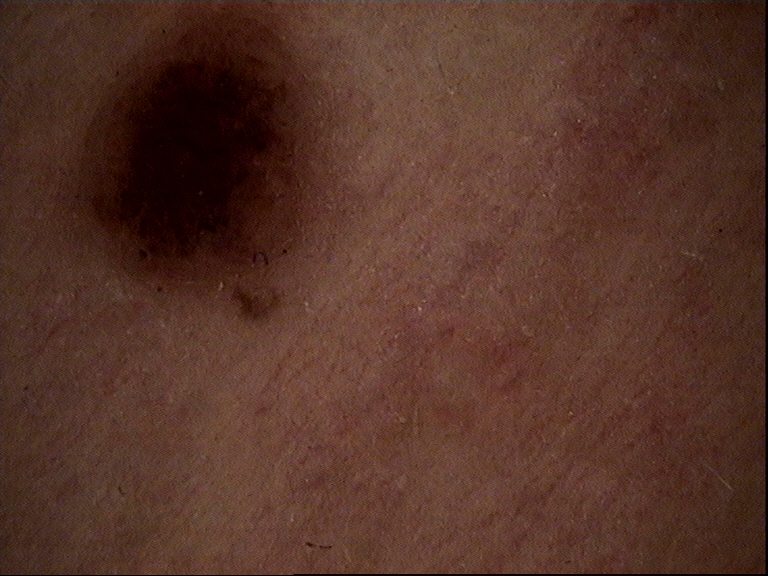A dermoscopy image of a single skin lesion. Classified as a benign lesion — a dysplastic junctional nevus.